A dermoscopy image of a single skin lesion.
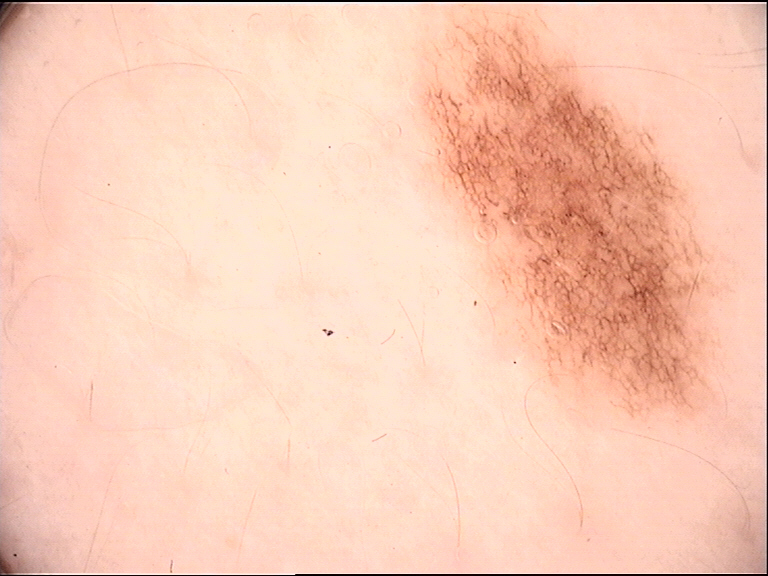Impression: Labeled as a benign lesion — a dysplastic junctional nevus.